The affected area is the arm; an image taken at an angle; texture is reported as raised or bumpy; reported lesion symptoms include itching; the patient notes the condition has been present for about one day; the patient considered this a rash:
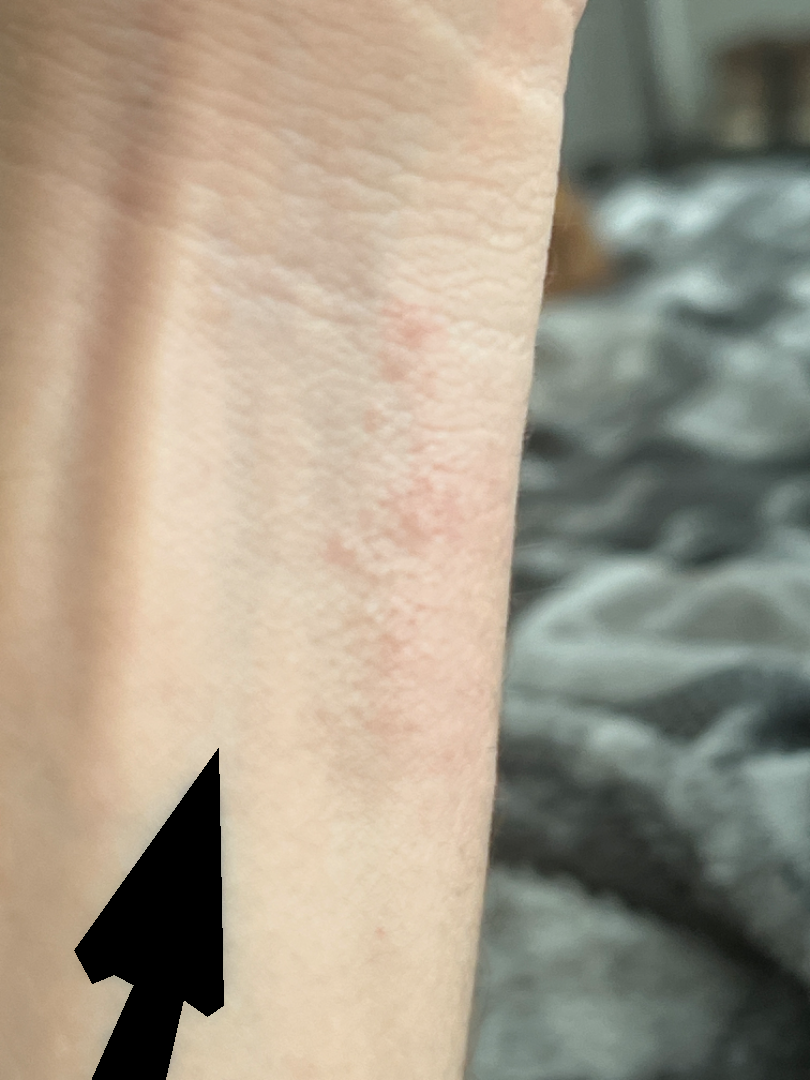Assessment: No differential diagnosis could be assigned on photographic review.